An image taken at a distance. The subject is a female aged 18–29. Reported duration is less than one week. Located on the arm. The patient notes the lesion is raised or bumpy. Self-categorized by the patient as acne. Fitzpatrick IV; lay reviewers estimated Monk Skin Tone 4 or 7 (two reviewer pools disagreed): 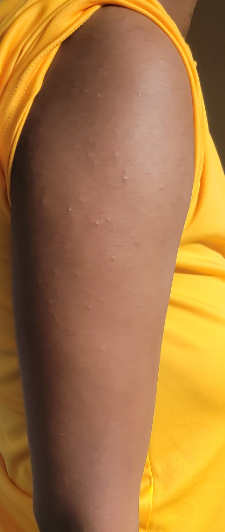dermatologist impression: the favored diagnosis is Keratosis pilaris; also raised was Folliculitis